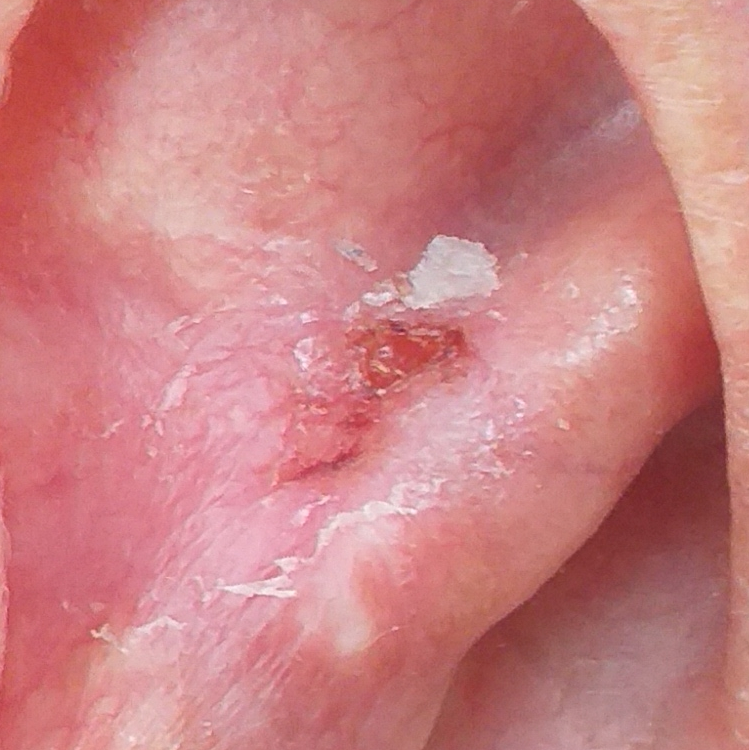Conclusion:
Confirmed on histopathology as a basal cell carcinoma.